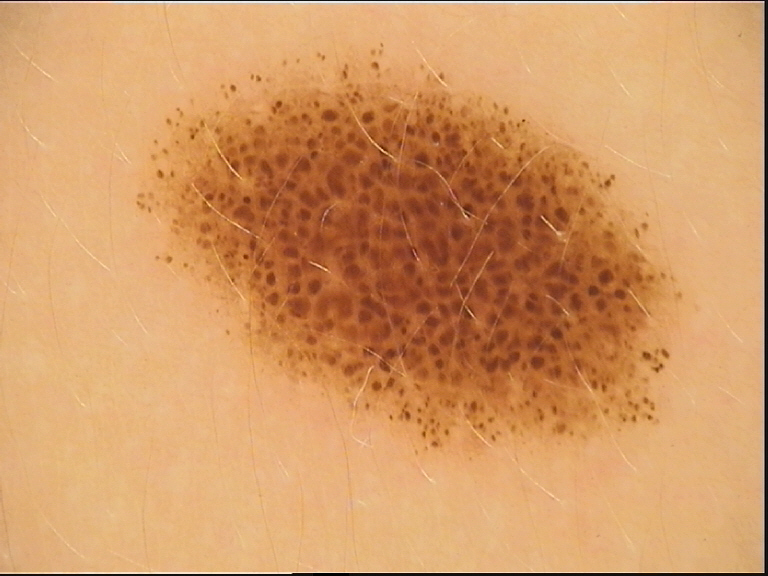Findings: A dermoscopic image of a skin lesion. Conclusion: Consistent with a dysplastic compound nevus.